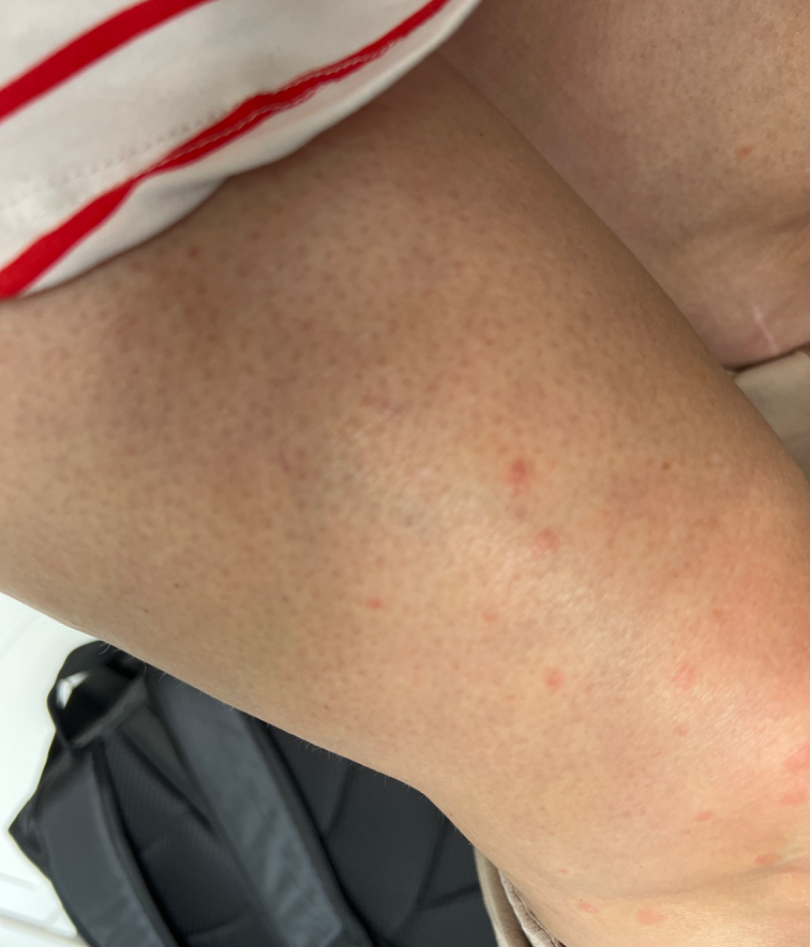contributor — female, age 40–49 | history — less than one week | photo taken — at a distance | self-categorized as — a rash | site — arm, leg and back of the hand | texture — raised or bumpy | differential — the reviewer's impression was Folliculitis.